Dermoscopy of a skin lesion: 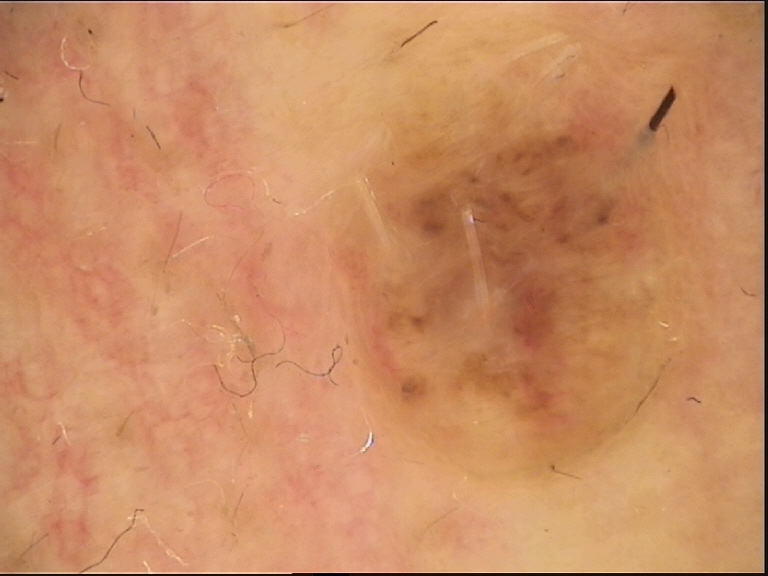class: dermal nevus (expert consensus)